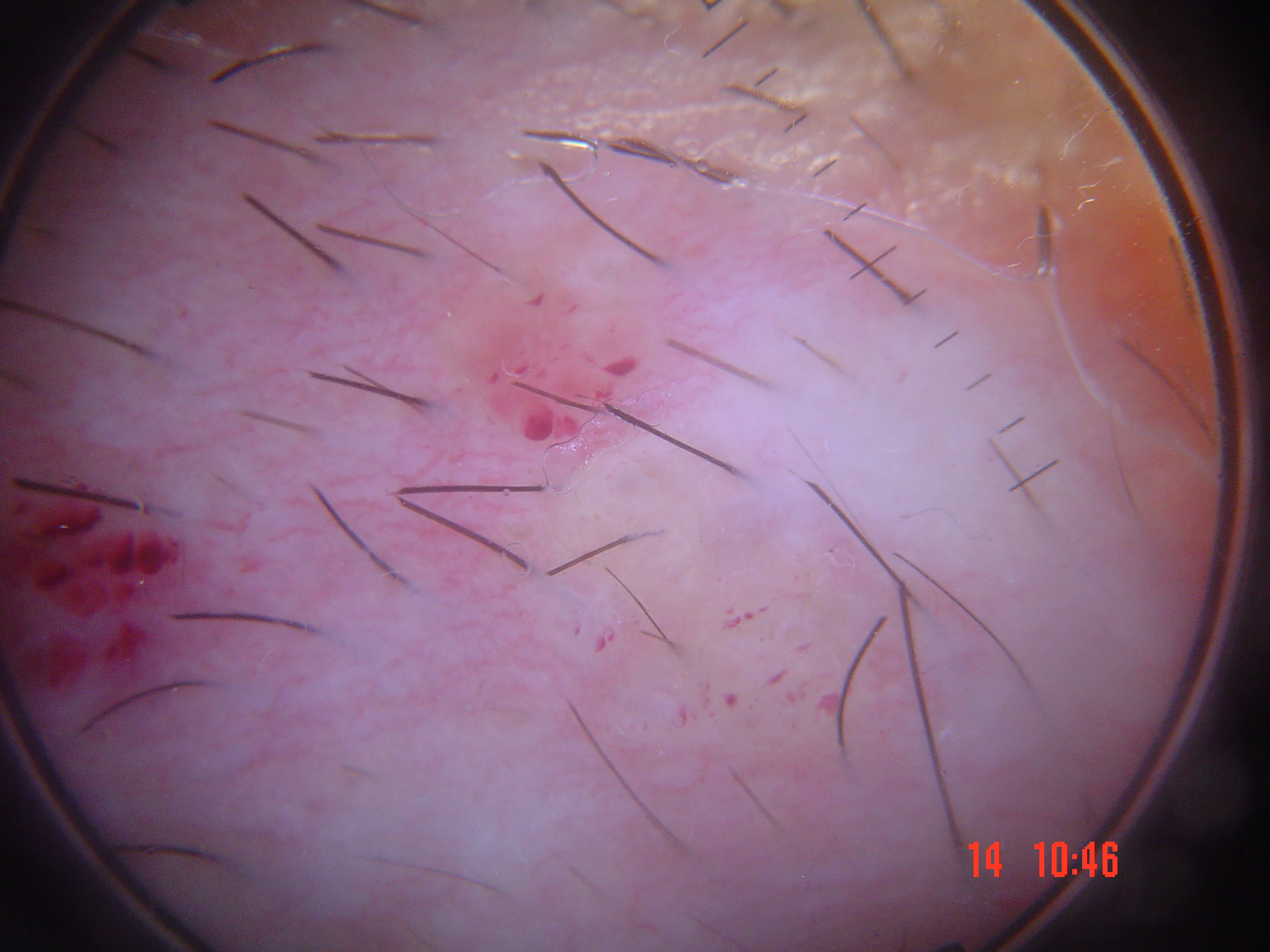subtype=vascular | diagnosis=lymphangioma (expert consensus).